Close-up view: 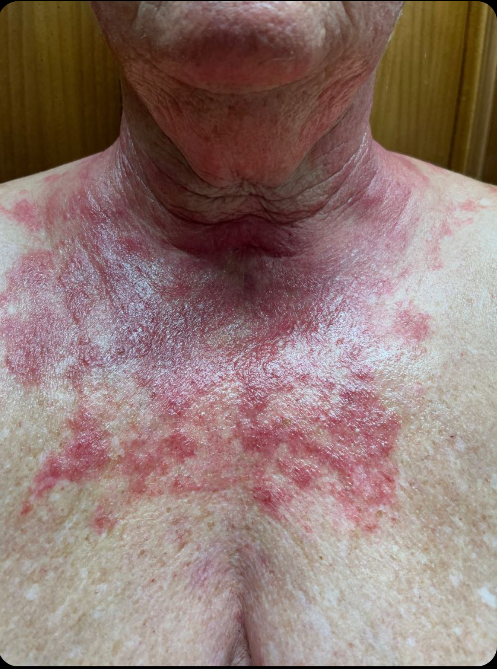| field | value |
|---|---|
| diagnostic considerations | Photodermatitis (0.33); Drug-induced photosensitivity (0.33); Irritant Contact Dermatitis (0.33) |